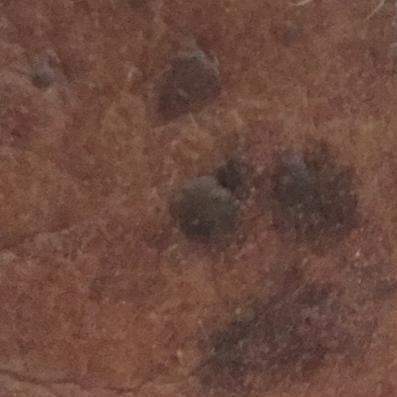Patient and lesion:
Located on the face. By the patient's account, the lesion is elevated.
Conclusion:
Consistent with a benign skin lesion — a seborrheic keratosis.